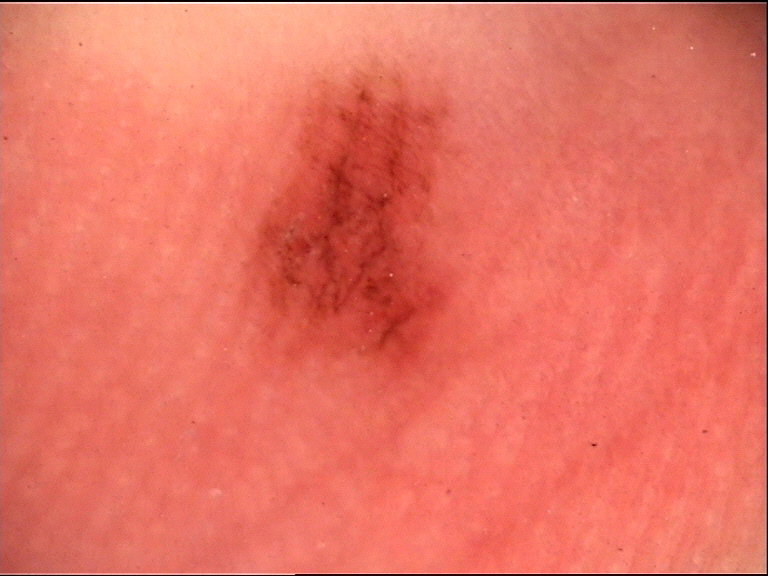Q: What was the diagnostic impression?
A: acral dysplastic junctional nevus (expert consensus)